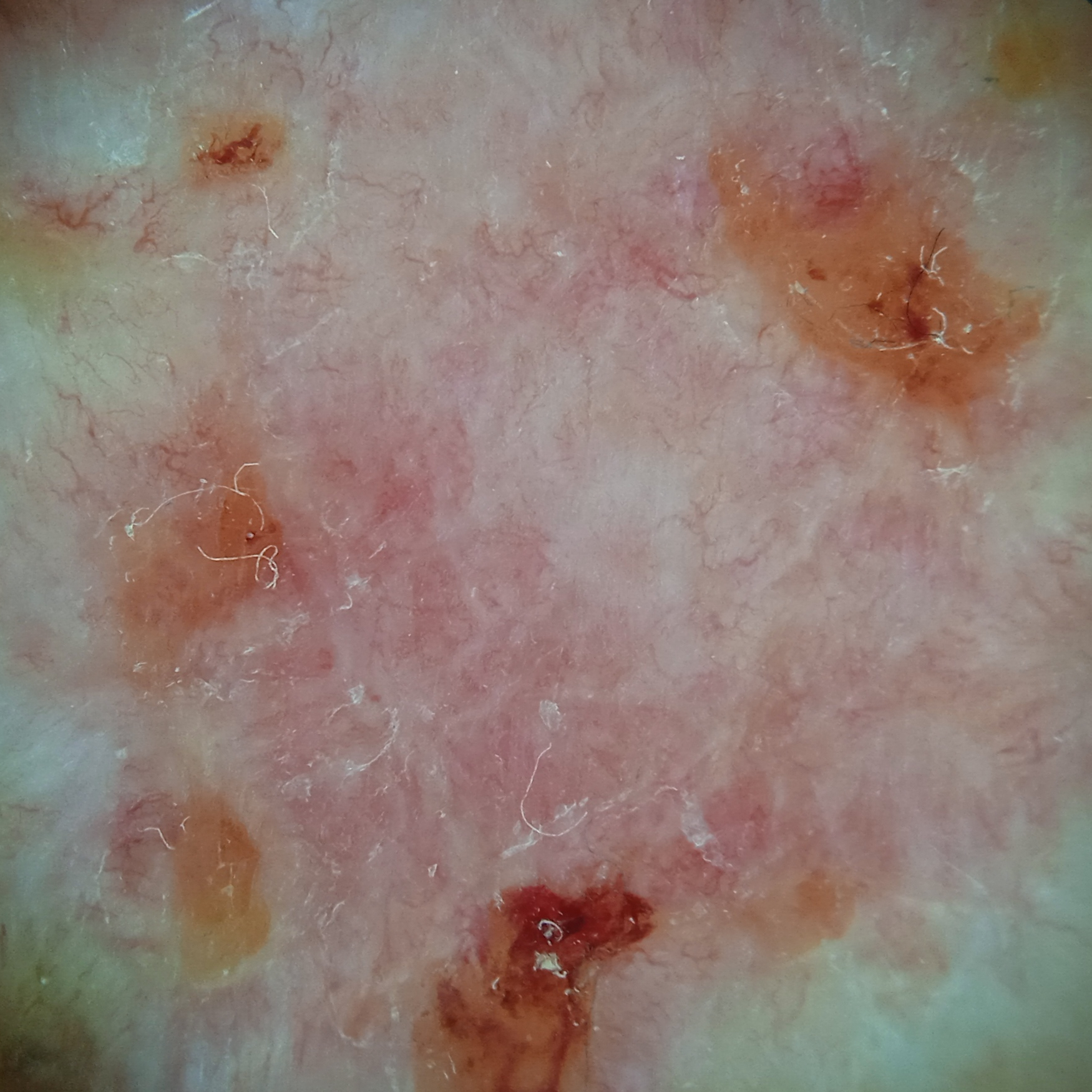imaging: dermatoscopic image | risk factors: a personal history of cancer, a family history of skin cancer | referral context: clinical suspicion of basal cell carcinoma | subject: male, age 81 | sun reaction: skin reddens with sun exposure | location: the back | diameter: 12.6 mm | diagnostic label: basal cell carcinoma (biopsy-proven).